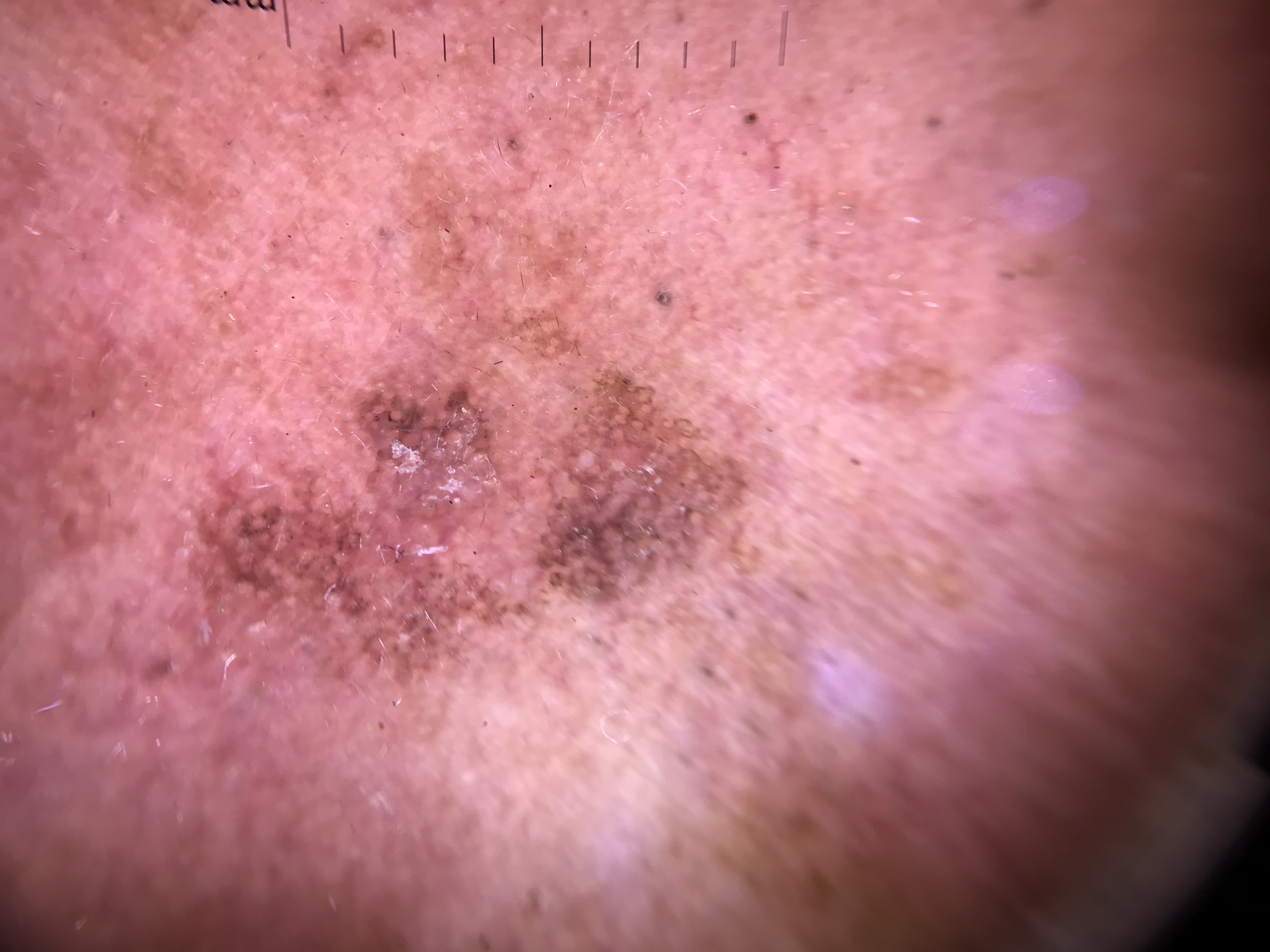A dermoscopy image of a single skin lesion.
The diagnostic label was a keratinocytic lesion — a seborrheic keratosis.